A female patient in their mid- to late 60s. A skin lesion imaged with contact-polarized dermoscopy — 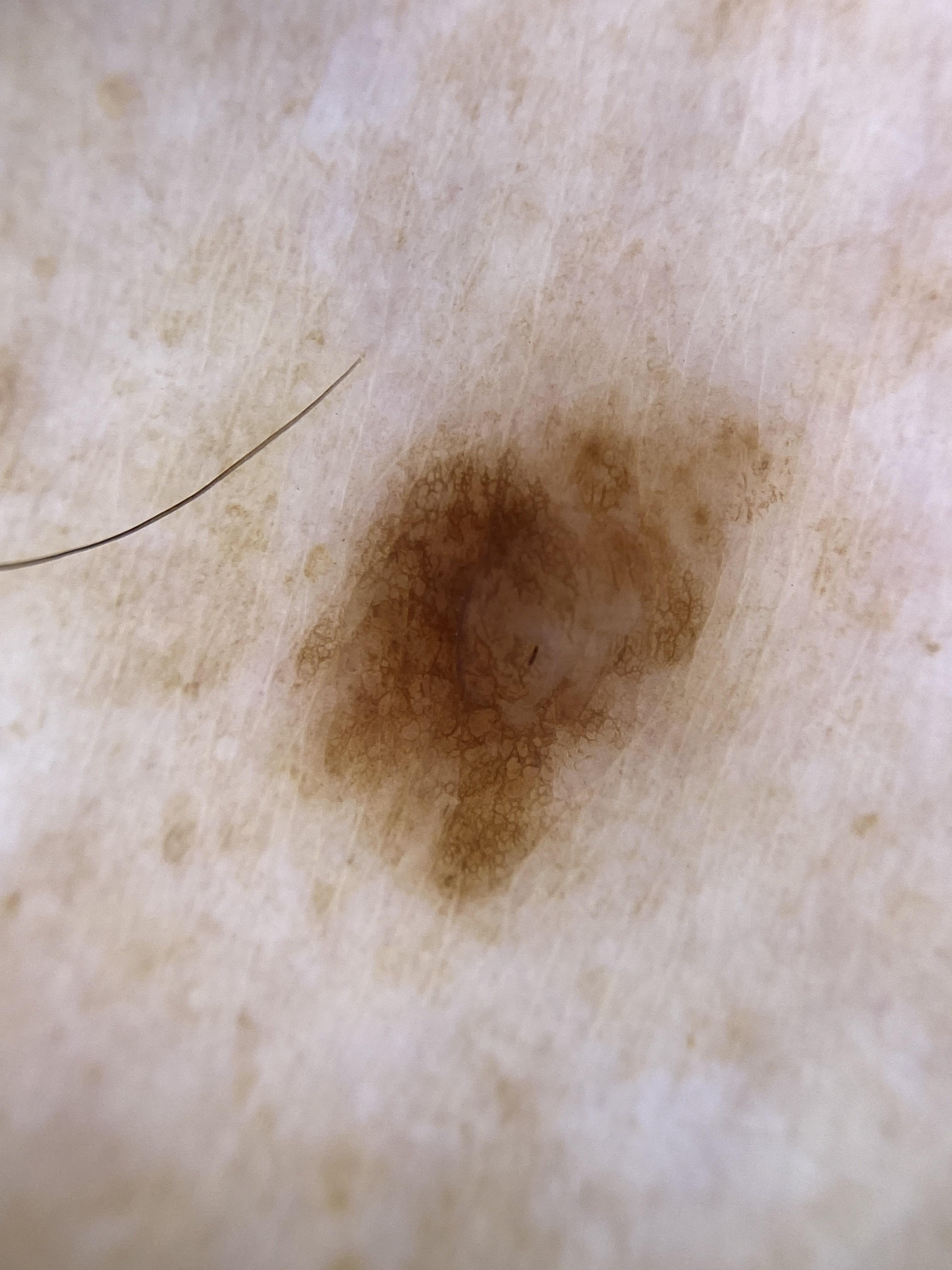body site: a lower extremity
diagnostic label: Nevus (clinical impression)